The affected area is the leg, front of the torso, arm and top or side of the foot; the patient reports the condition has been present for about one day; this image was taken at a distance; symptoms reported: itching; the lesion is described as raised or bumpy; the patient is 18–29, female; associated systemic symptoms include fatigue and shortness of breath:
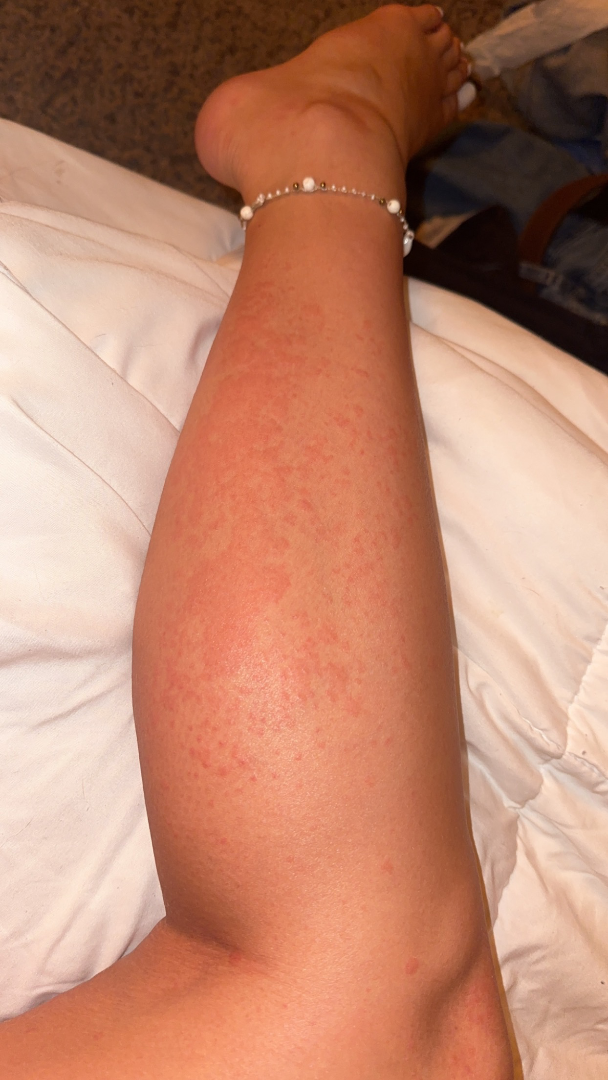assessment=the leading impression is Allergic Contact Dermatitis; also raised was Urticaria; a more distant consideration is Eczema